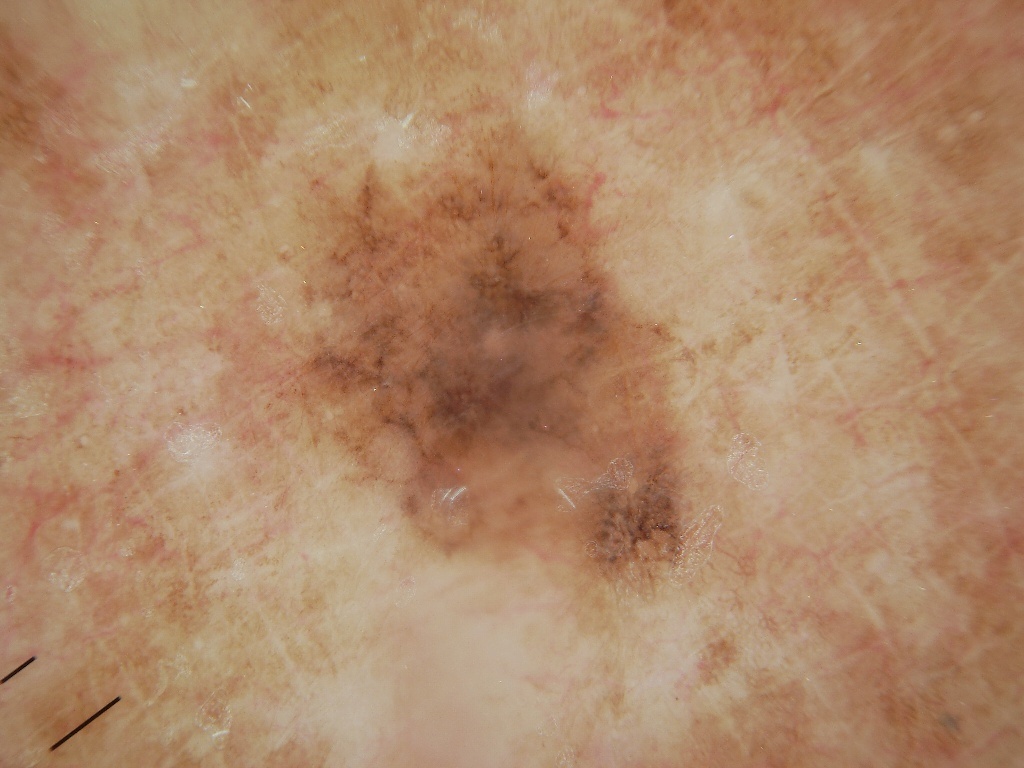Image and clinical context: A dermoscopic image of a skin lesion. The patient is a female about 70 years old. The lesion takes up a moderate portion of the field. The visible lesion spans 205 88 697 609. Dermoscopic review identifies pigment network. Conclusion: On biopsy, the diagnosis was a melanoma.